The photo was captured at a distance; the leg and arm are involved: 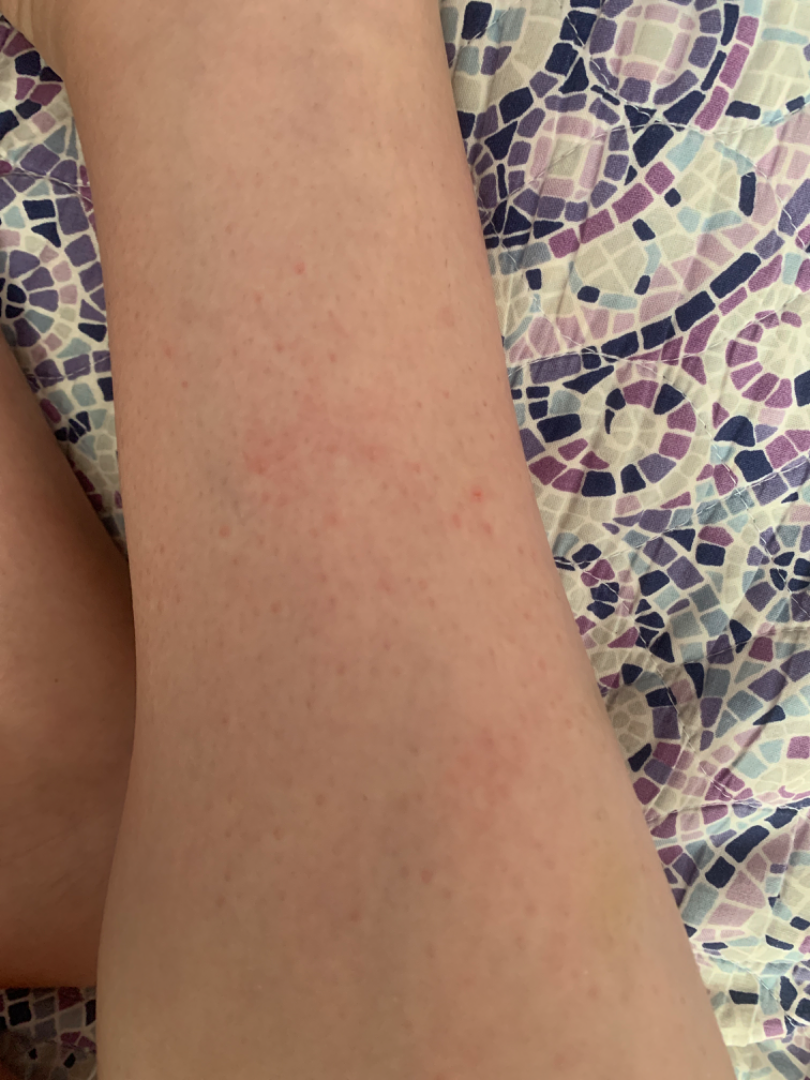{"assessment": "unable to determine"}